A close-up photograph; the lesion involves the leg; the subject is female:
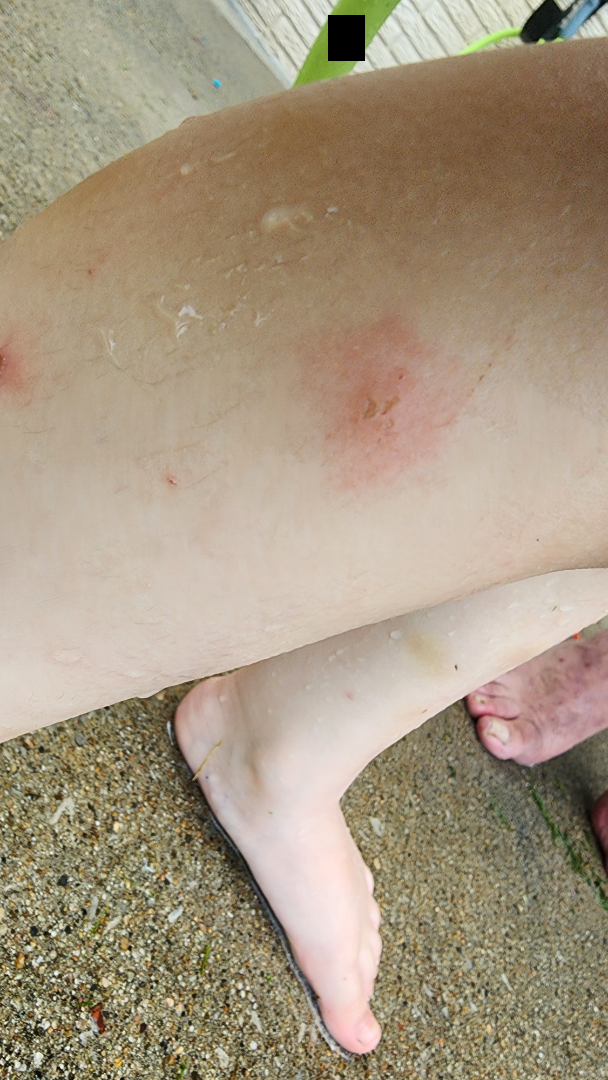Case summary:
– assessment — reviewed remotely by three dermatologists: most consistent with Insect Bite; the differential also includes Eczema; with consideration of Acute dermatitis, NOS; less likely is Skin infection; less probable is Contact dermatitis, NOS